The patient indicates associated fatigue. Texture is reported as flat. No associated lesion symptoms were reported. Present for less than one week. A close-up photograph. Female subject, age 50–59. The affected area is the leg: 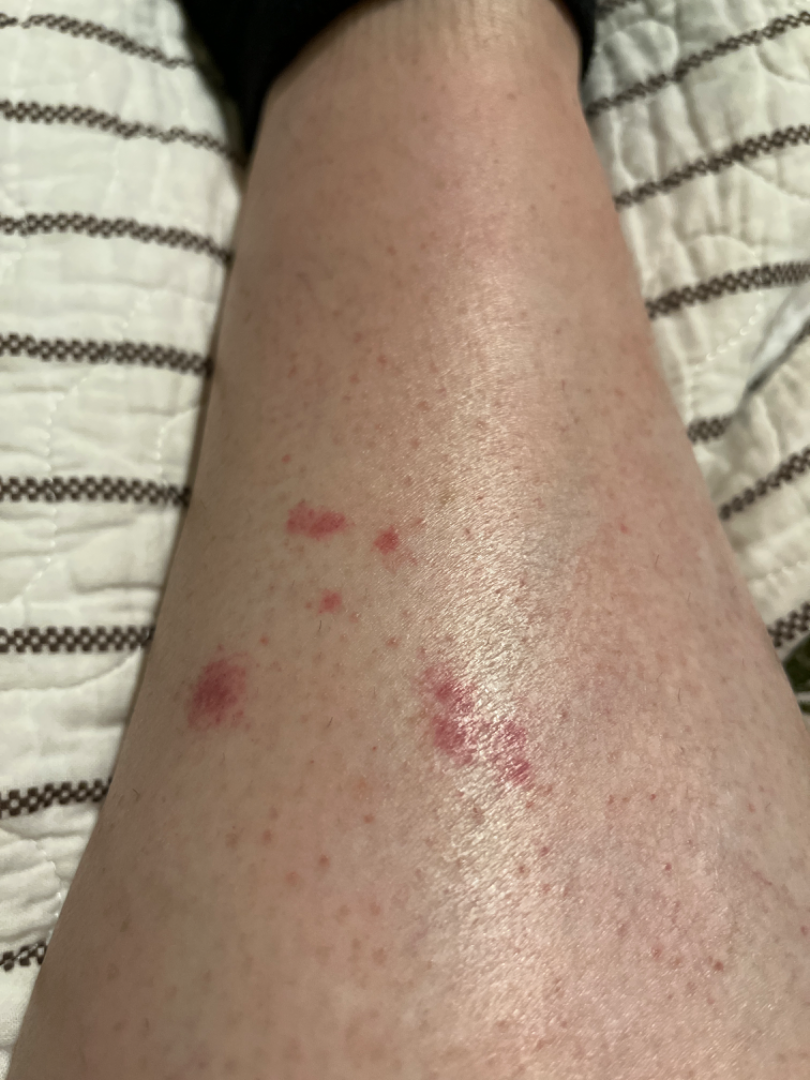Notes:
* diagnostic considerations — three dermatologists each reviewed the case: most consistent with Pigmented purpuric eruption; also raised was Insect Bite; less likely is Allergic Contact Dermatitis; less probable is Purpura